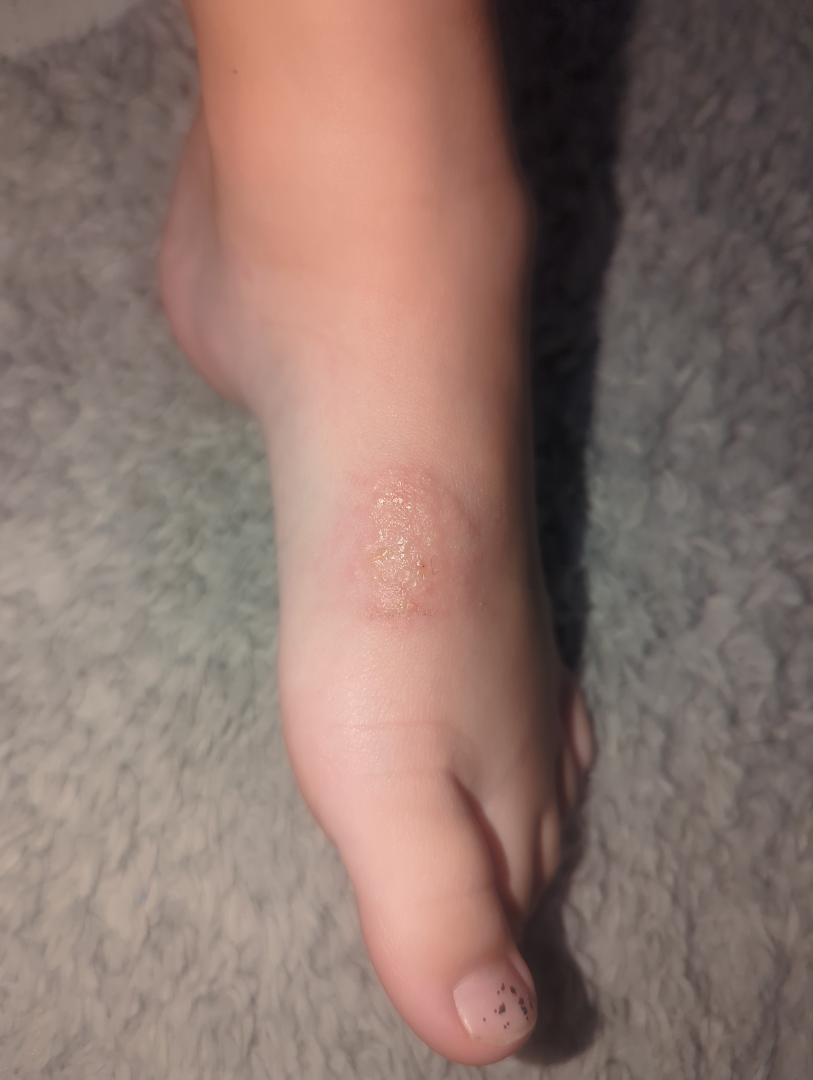Notes:
• assessment · reviewed remotely by one dermatologist: the differential is split between Eczema and Allergic Contact Dermatitis